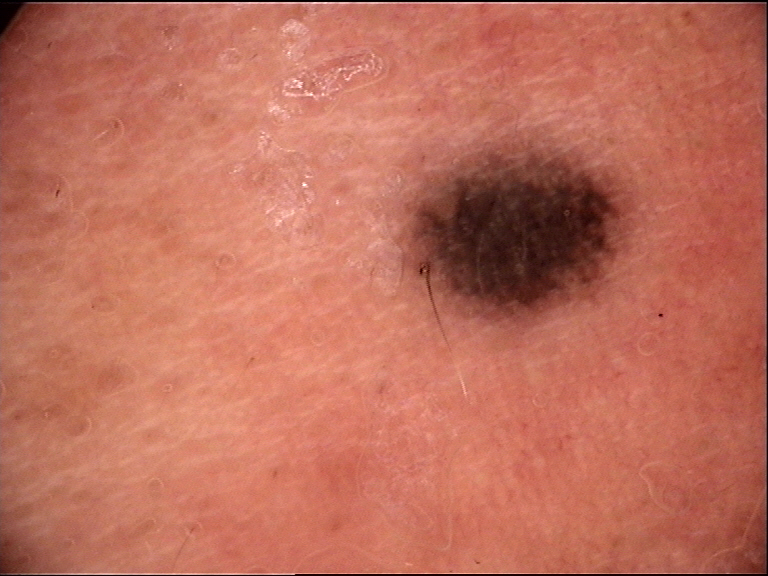{
  "image": "dermoscopy",
  "diagnosis": {
    "name": "blue nevus",
    "code": "bdb",
    "malignancy": "benign",
    "super_class": "melanocytic",
    "confirmation": "expert consensus"
  }
}